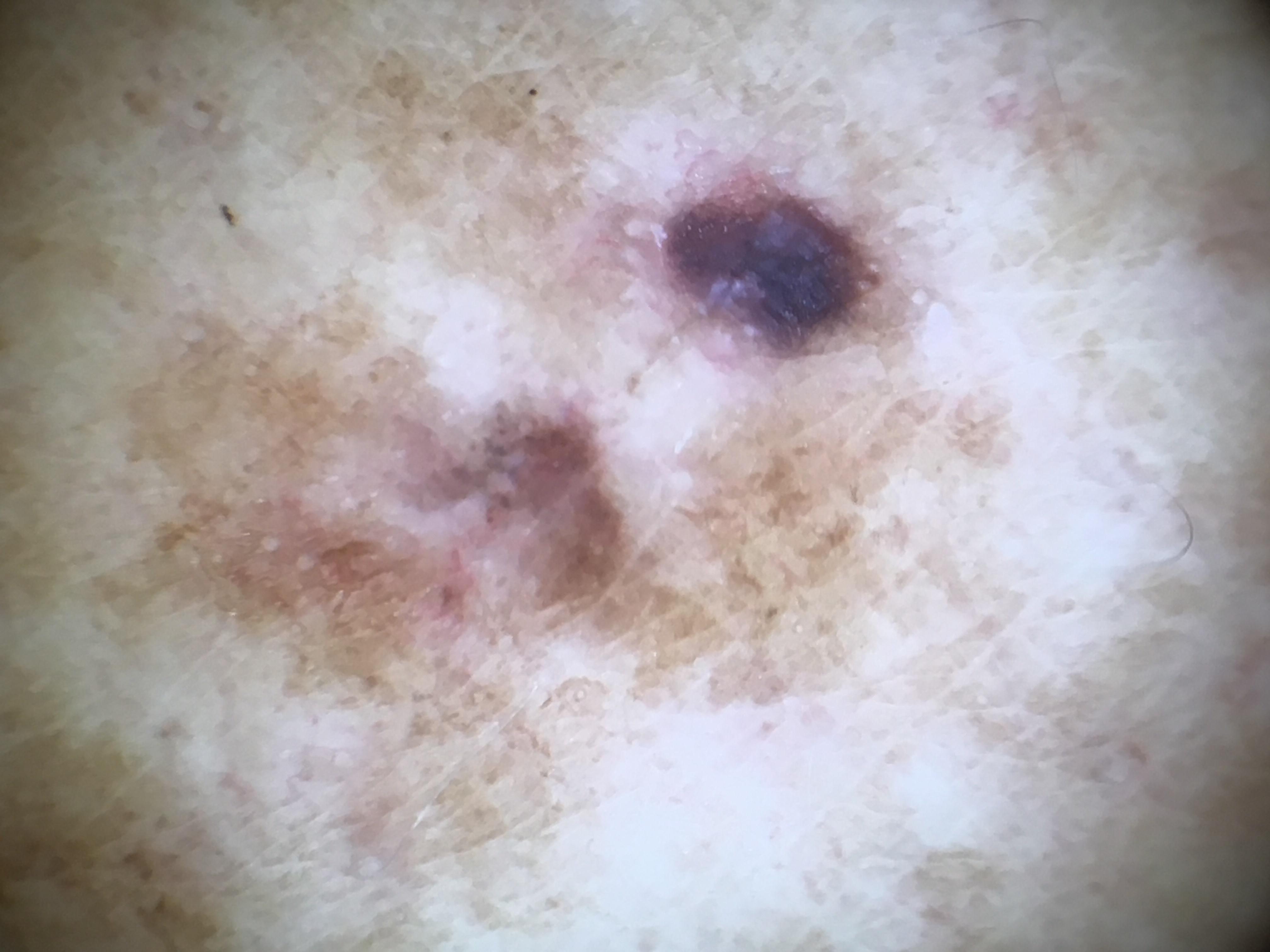Conclusion: Histopathology confirmed a melanoma.